A dermoscopic photograph of a skin lesion.
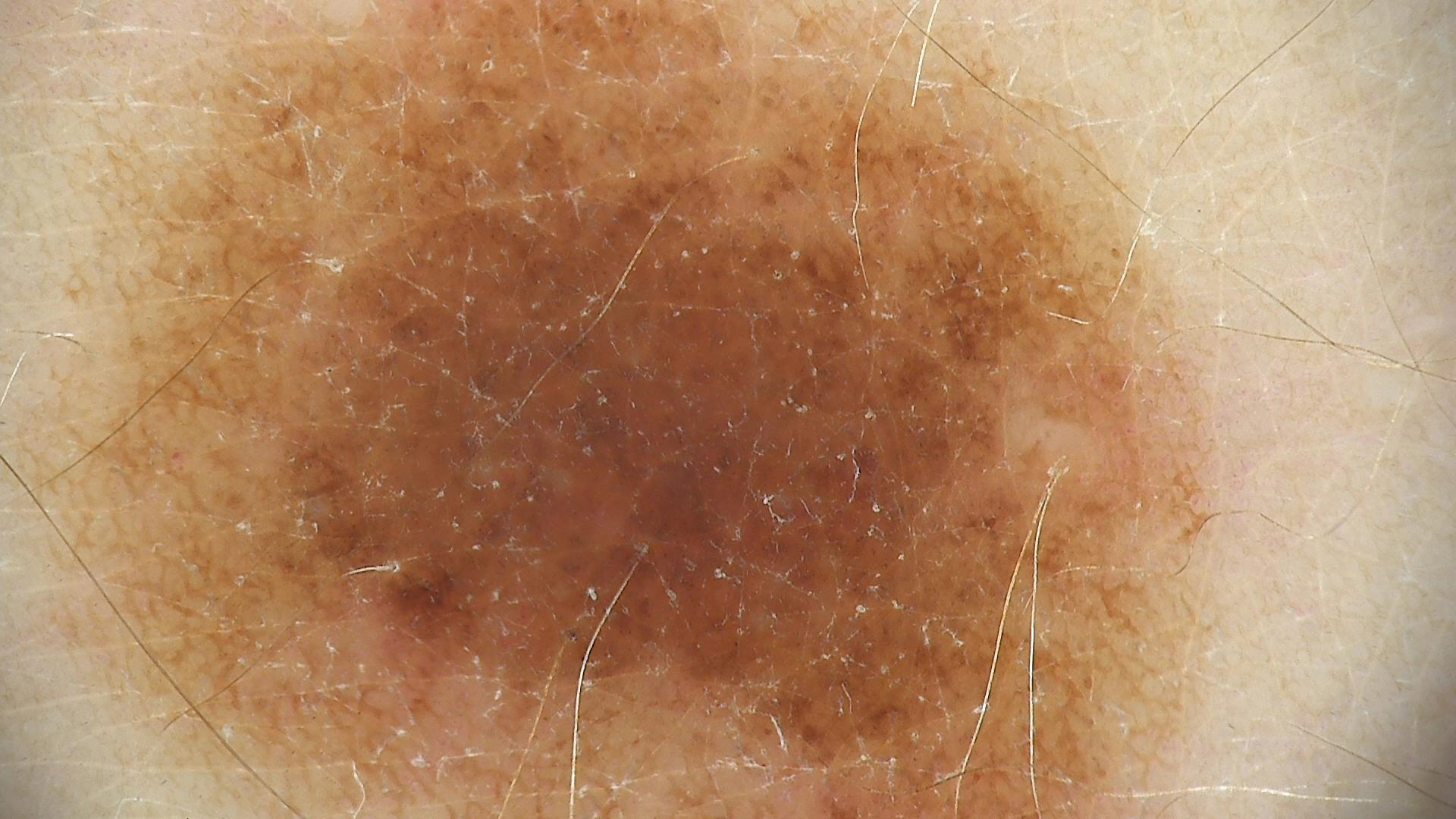diagnosis = dysplastic junctional nevus (expert consensus).